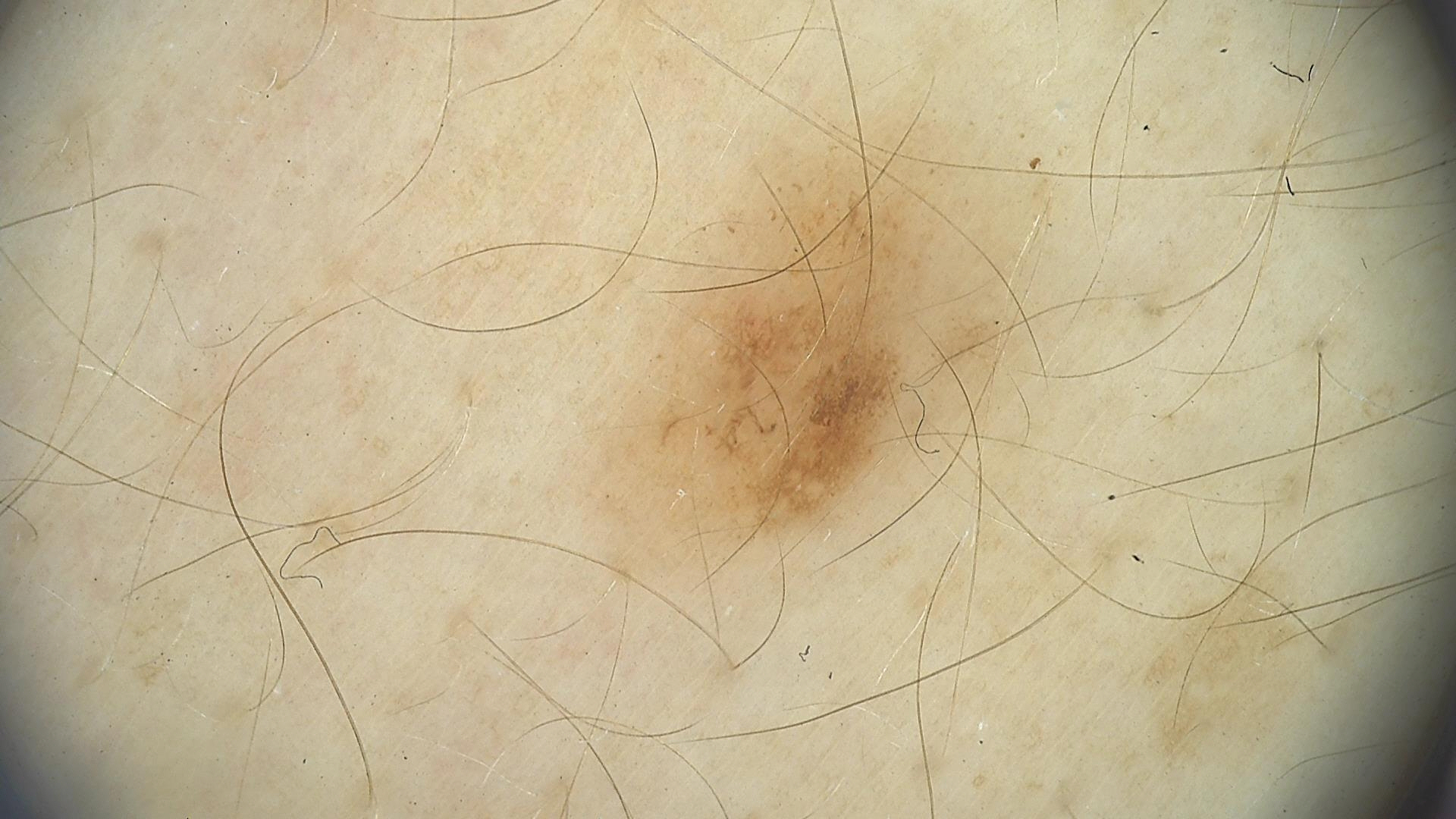A dermoscopy image of a single skin lesion. Classified as a benign lesion — a dysplastic junctional nevus.